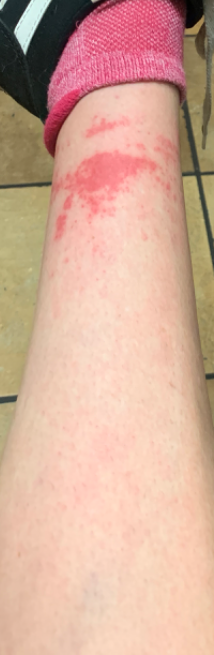| field | value |
|---|---|
| image framing | at a distance |
| contributor | female, age 50–59 |
| affected area | leg |
| dermatologist impression | the differential includes Stasis Dermatitis; Acute dermatitis, NOS; and Leukocytoclastic Vasculitis, with no clear leading consideration |